Reported duration is one to four weeks. A close-up photograph. Located on the arm. The patient described the issue as a rash:
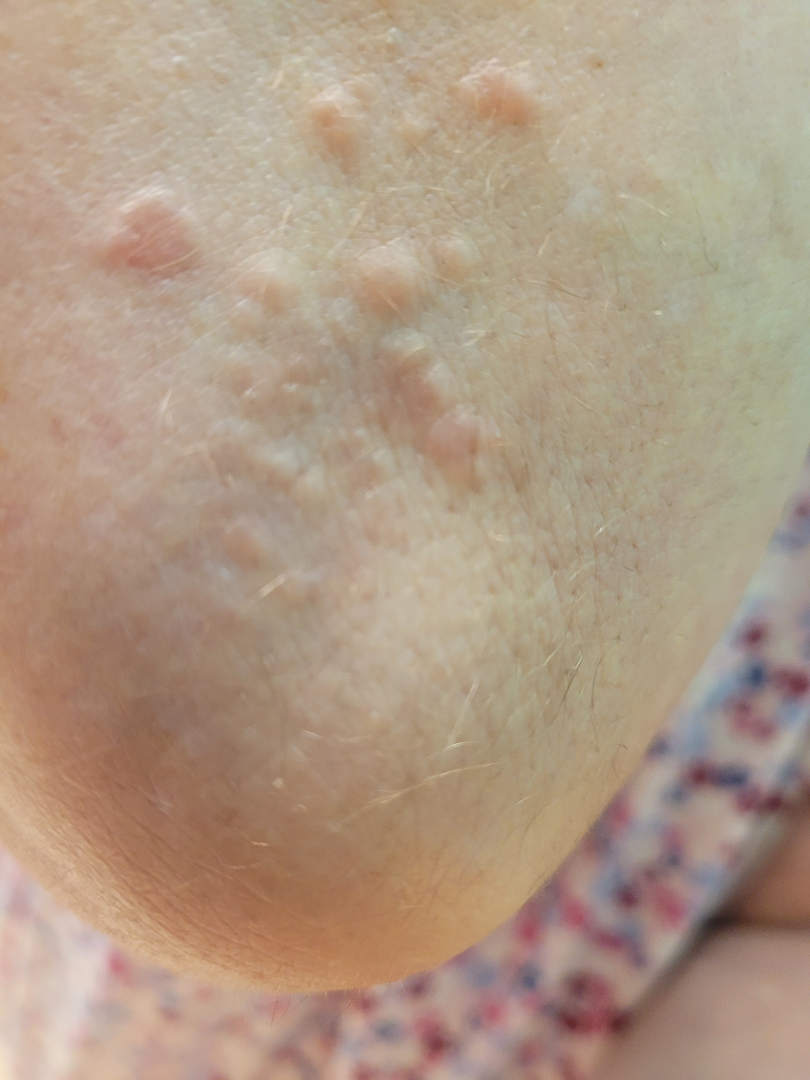  assessment: could not be assessed